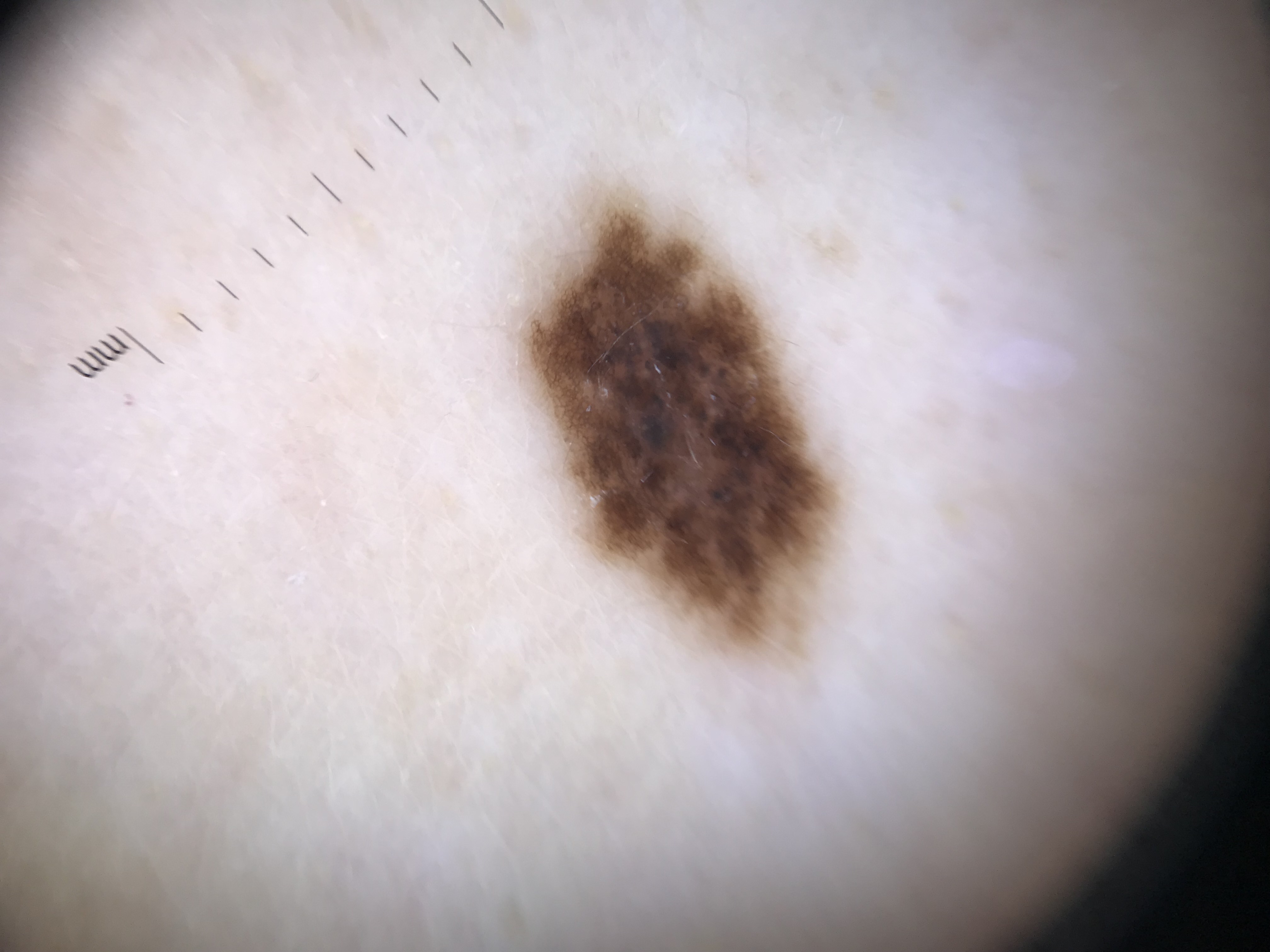A skin lesion imaged with a dermatoscope. The diagnostic label was a banal lesion — a congenital compound nevus.